The patient considered this a rash · the head or neck is involved · close-up view · the lesion is associated with itching, bothersome appearance and enlargement · skin tone: FST IV; non-clinician graders estimated Monk skin tone scale 3 or 4 · the patient notes the lesion is raised or bumpy:
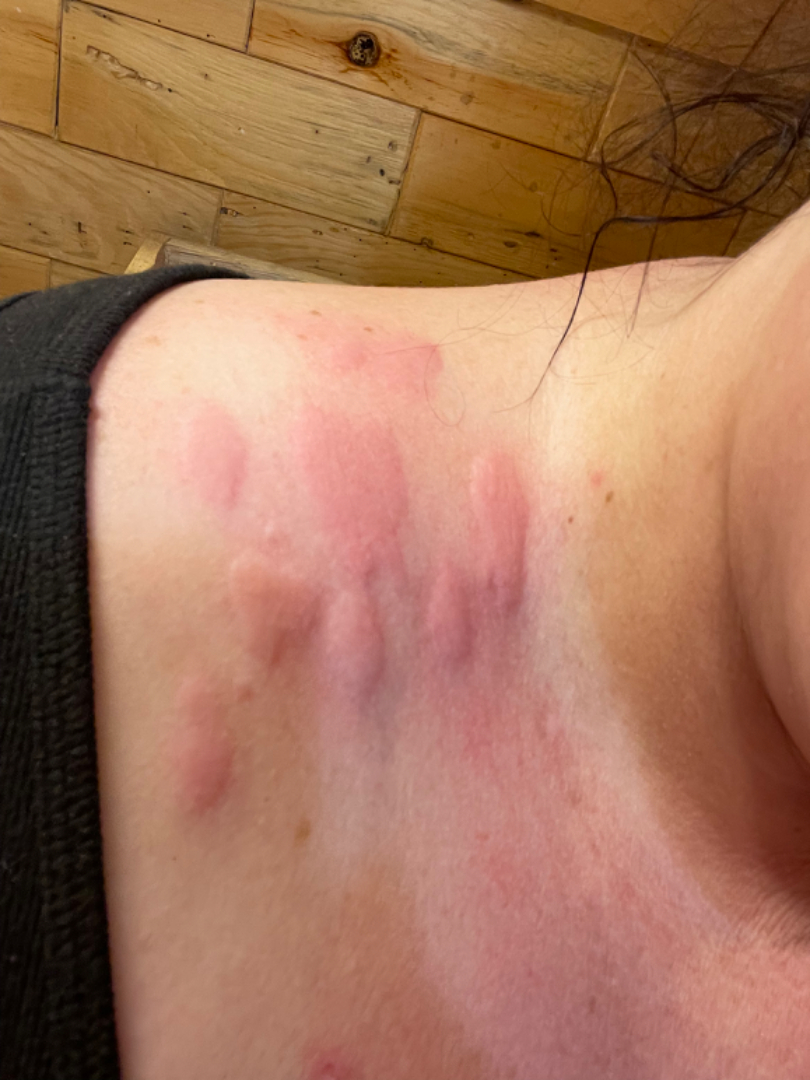Findings:
- assessment — a single dermatologist reviewed the case: most consistent with Urticaria